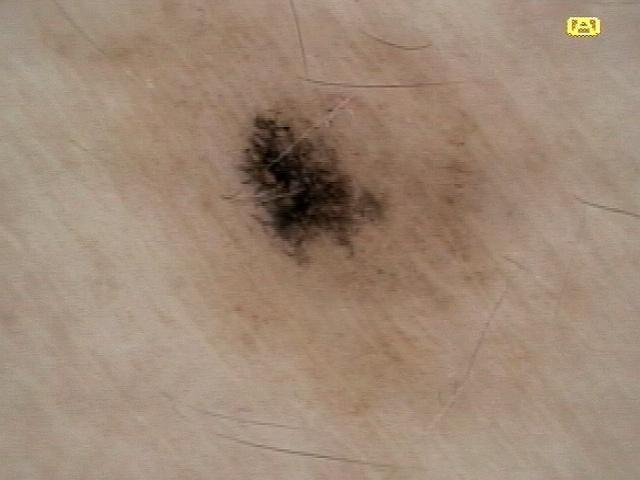Case:
* Fitzpatrick — II
* imaging — contact-polarized dermoscopy
* patient — male, about 40 years old
* location — the trunk
* pathology — Nevus (biopsy-proven)